The photo was captured at an angle — 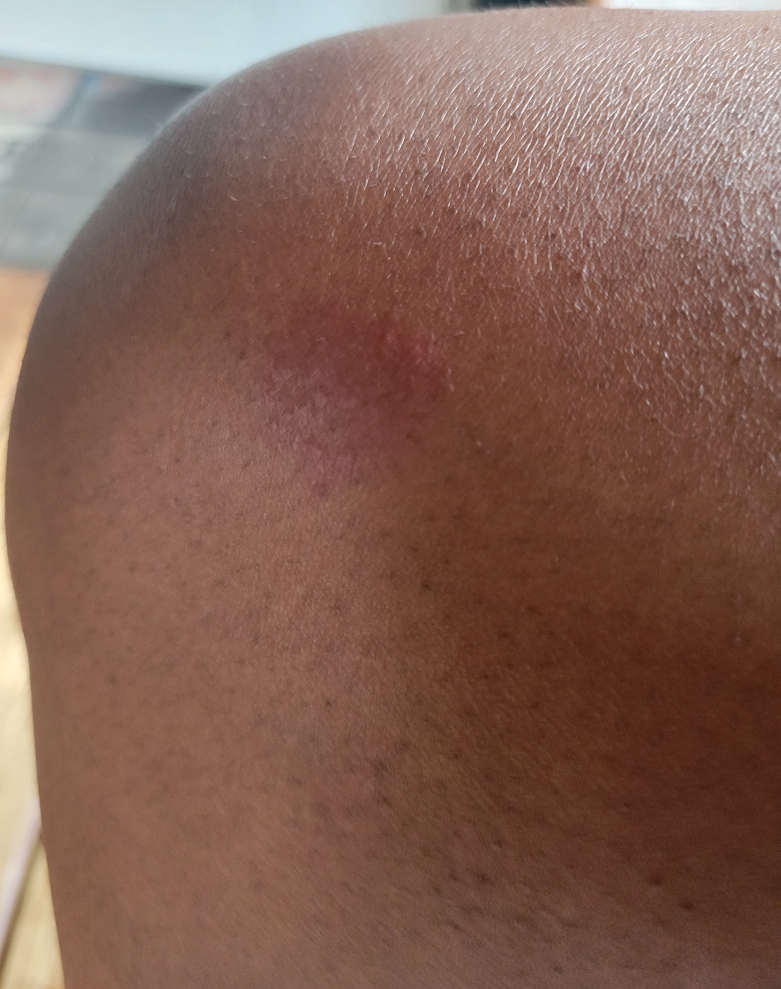Notes:
• assessment · ungradable on photographic review